The patient is Fitzpatrick skin type II · the chart records prior malignancy (patient or family) and no tobacco use · a smartphone photograph of a skin lesion · a female patient 78 years of age:
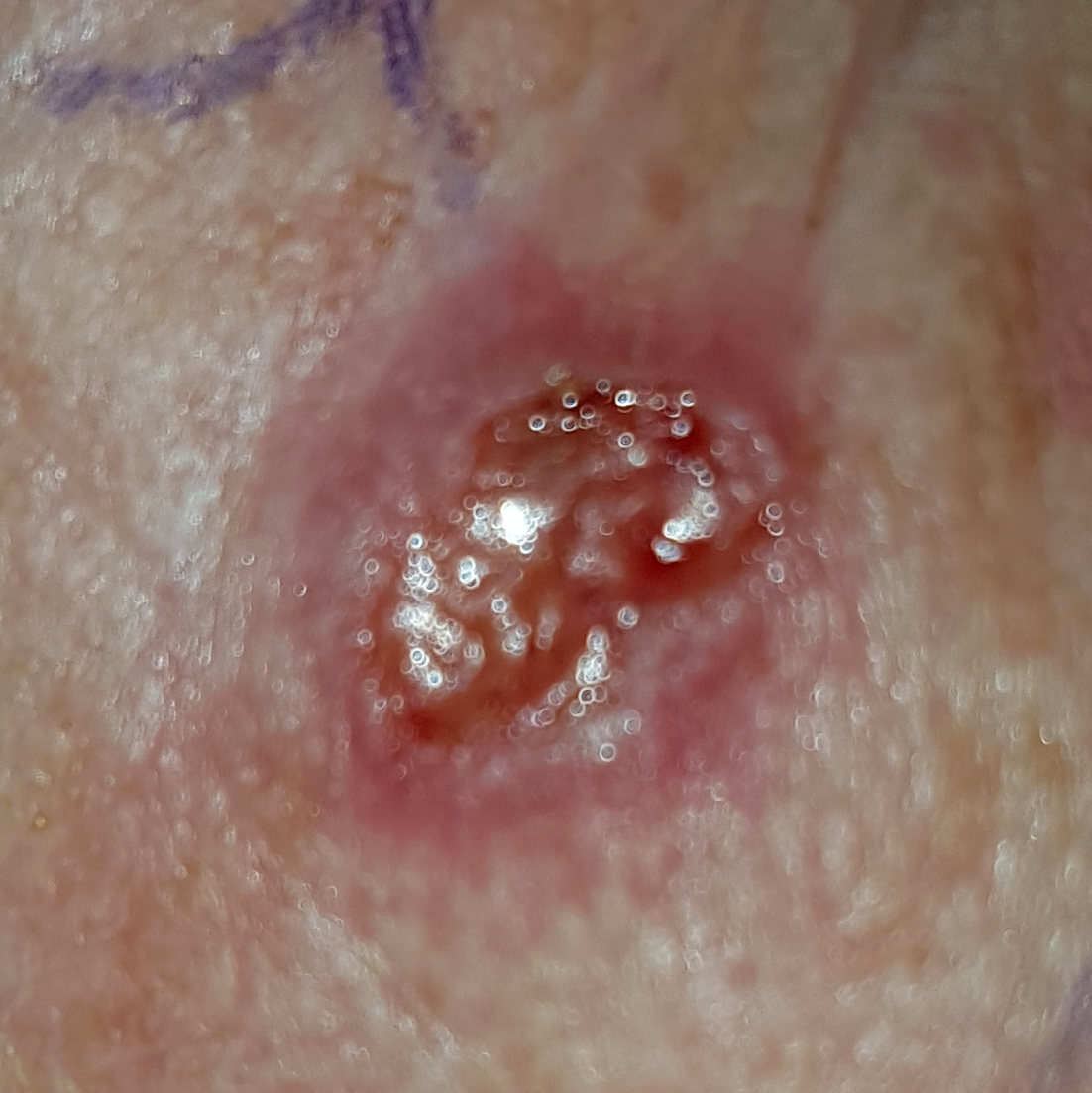* body site · the face
* lesion size · approx. 10 × 6 mm
* diagnostic label · basal cell carcinoma (biopsy-proven)